Recorded as Fitzpatrick phototype II: 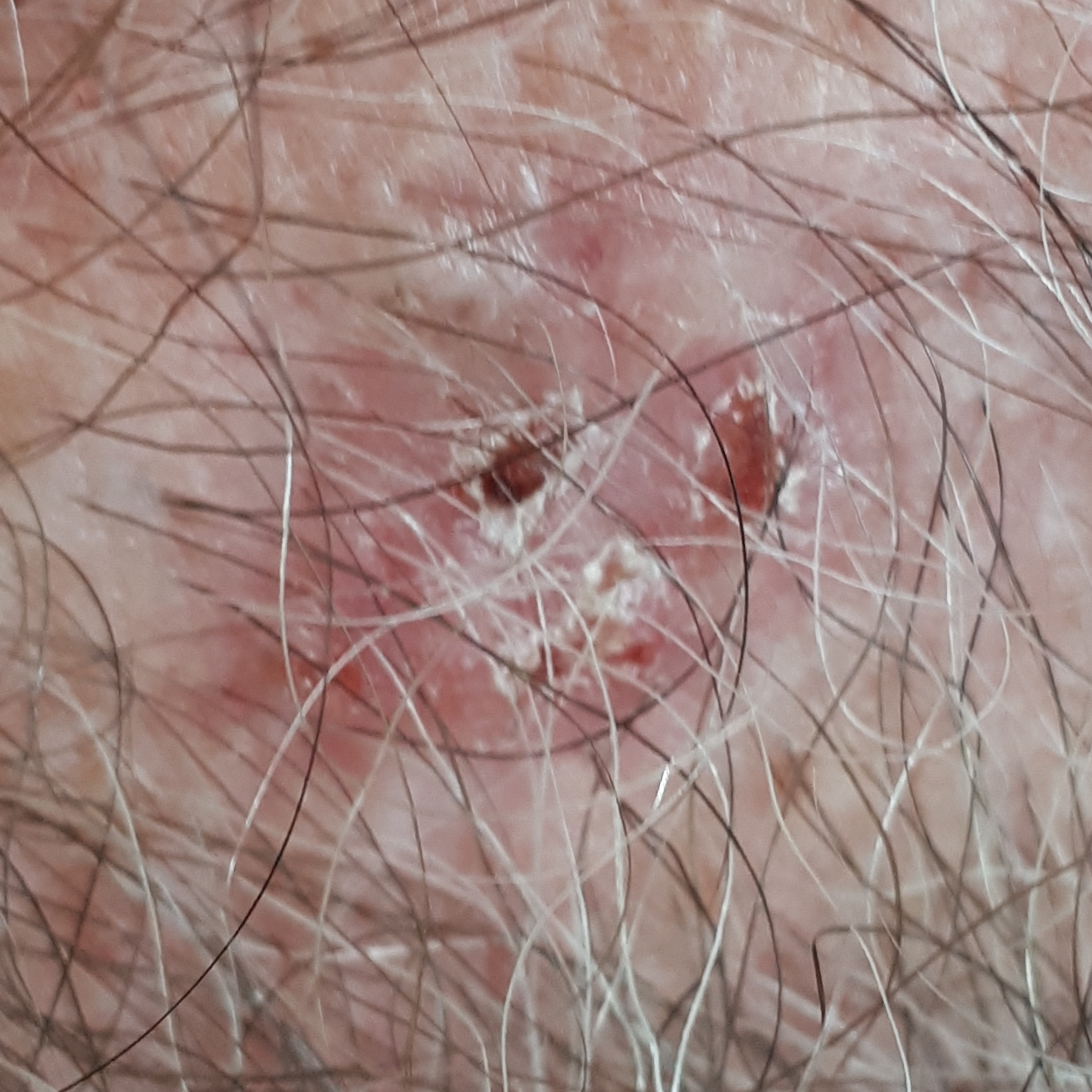Summary:
The lesion is on the chest. By the patient's account, the lesion has bled, has grown, and has changed, but does not itch and is not elevated.
Conclusion:
The biopsy diagnosis was a basal cell carcinoma.